A female subject approximately 80 years of age. A dermoscopic close-up of a skin lesion.
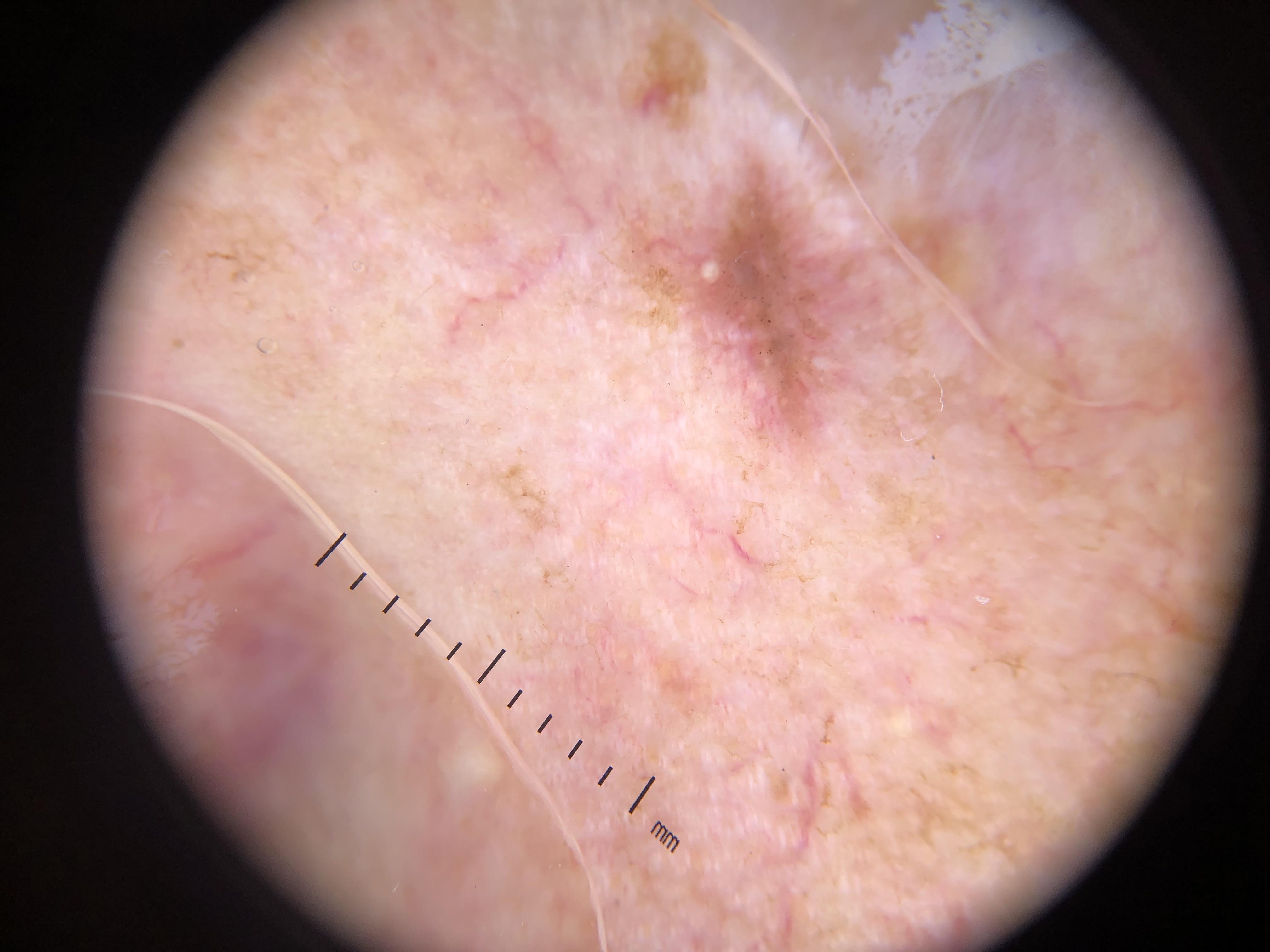location = the head or neck
diagnosis = Basal cell carcinoma (biopsy-proven)